A close-up photograph · located on the back of the hand:
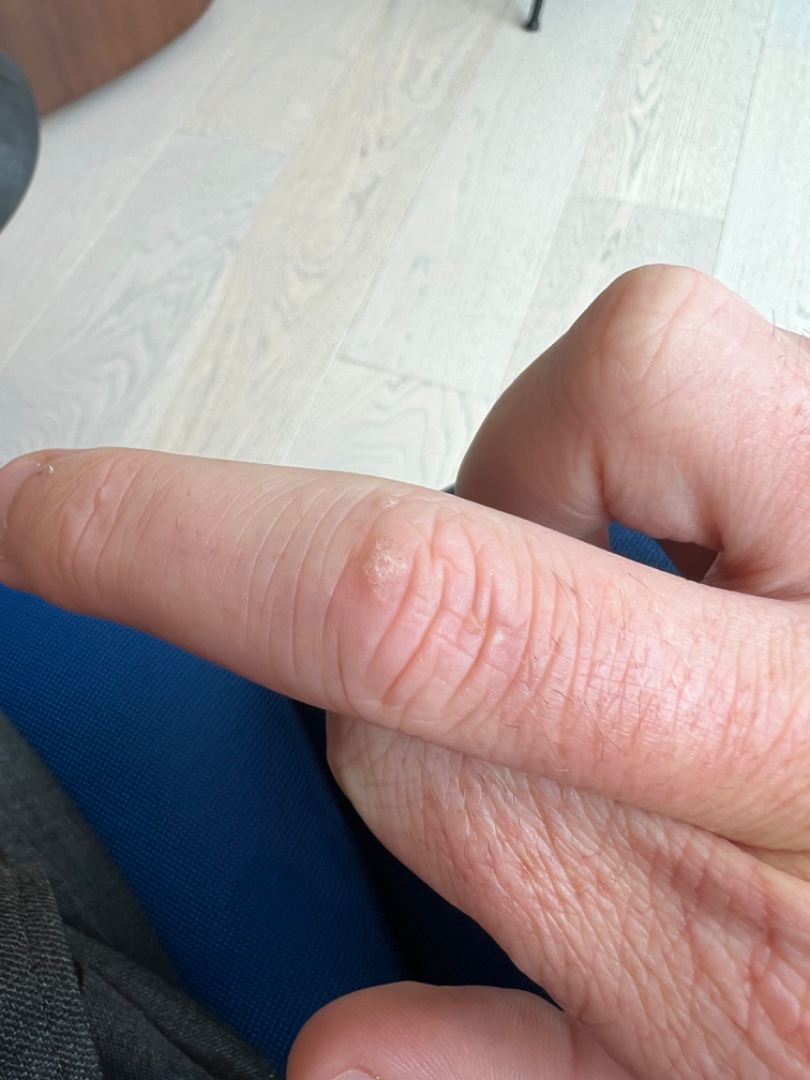Q: What is the differential diagnosis?
A: in keeping with Verruca vulgaris